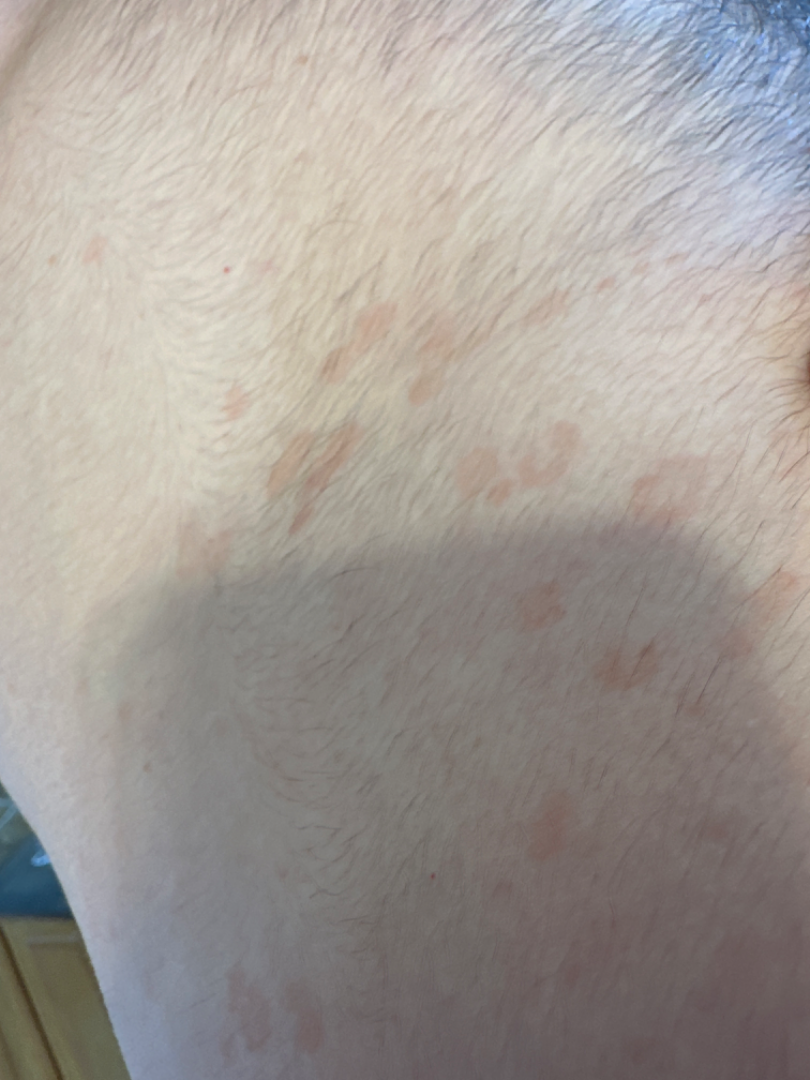Clinical context:
Located on the front of the torso and back of the torso. Close-up view.
Assessment:
Most consistent with Pityriasis rosea.